A female subject 75 years old · a clinical photograph of a skin lesion — 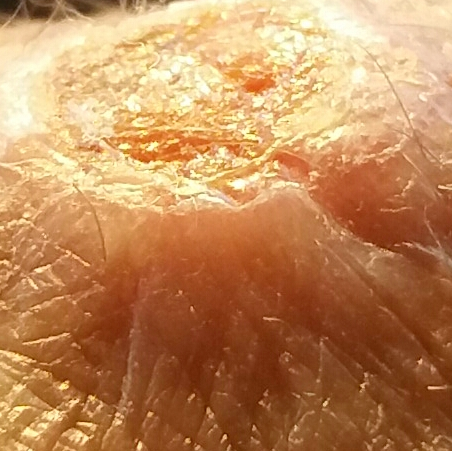Per patient report, the lesion is elevated, has grown, and has bled, but does not hurt and does not itch. On biopsy, the diagnosis was a basal cell carcinoma.